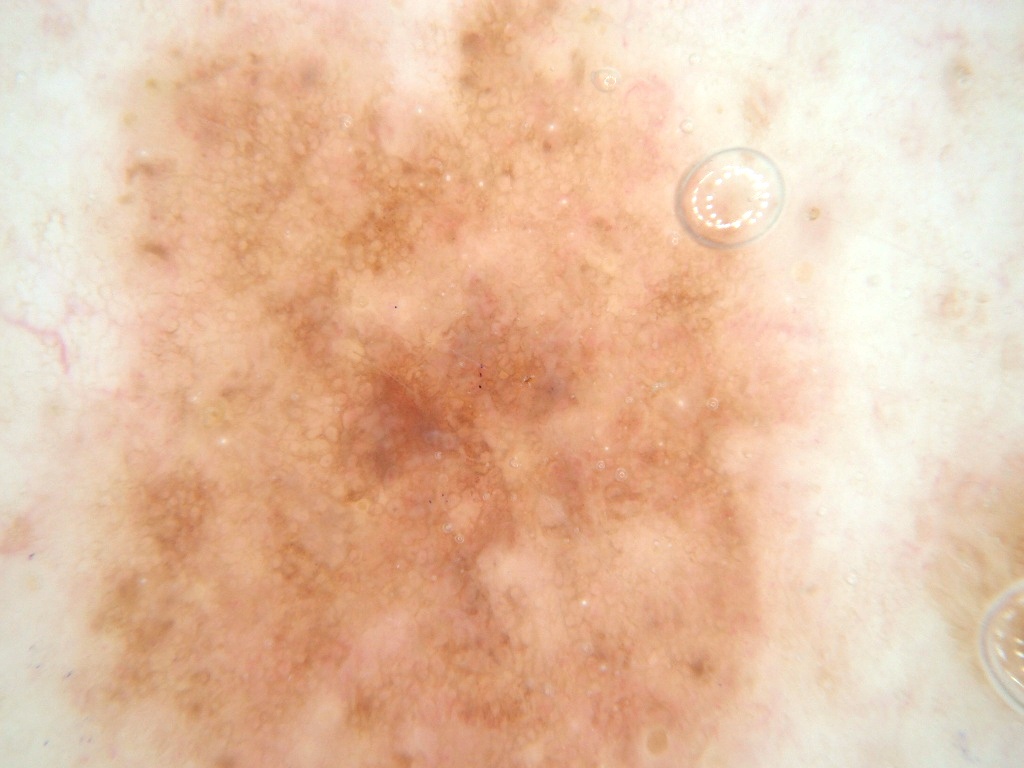<case>
  <image>
    <modality>dermoscopy</modality>
  </image>
  <lesion_location>
    <bbox_xyxy>0, 0, 843, 766</bbox_xyxy>
  </lesion_location>
  <diagnosis>
    <malignancy>benign</malignancy>
    <provenance>clinical</provenance>
  </diagnosis>
</case>